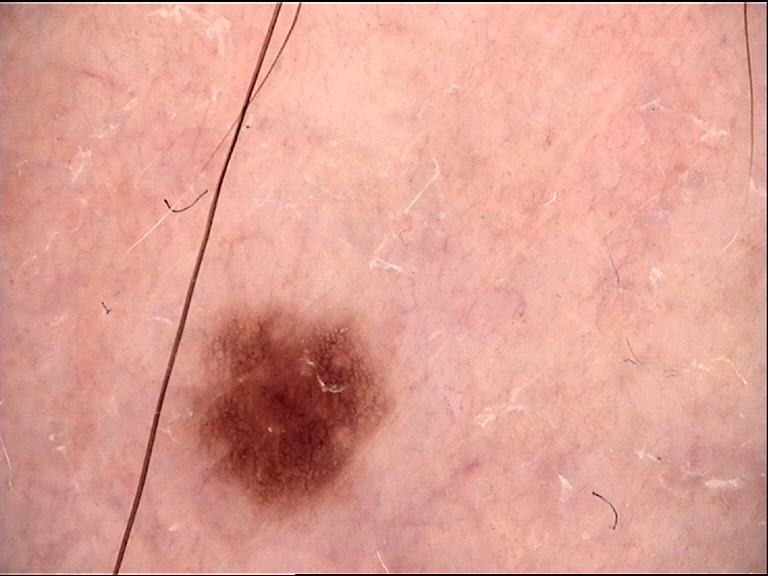modality = dermatoscopy | assessment = dysplastic junctional nevus (expert consensus).